The back of the hand is involved · the photograph was taken at an angle · the patient is a male aged 40–49 · the condition has been present for since childhood · Fitzpatrick skin type II · no associated lesion symptoms were reported · the patient notes the lesion is flat · no constitutional symptoms were reported:
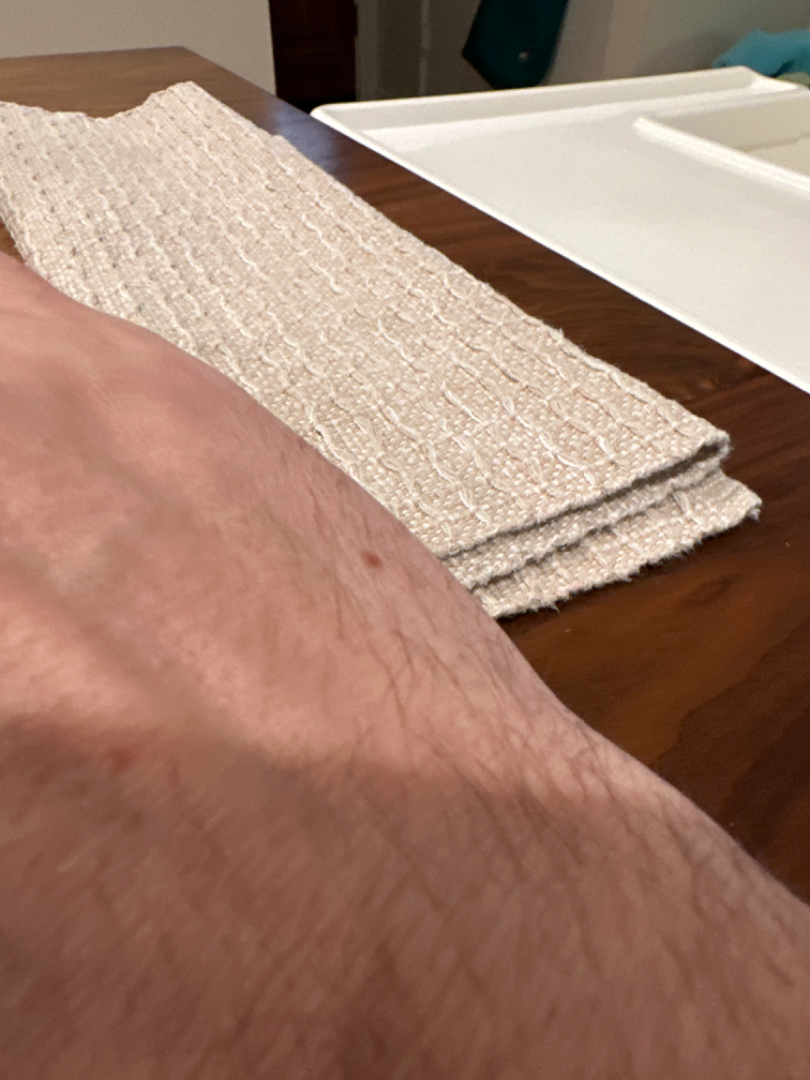Review: A single dermatologist reviewed the case: the differential includes Melanocytic Nevus and Atypical Nevus, with no clear leading consideration.